This image was taken at a distance.
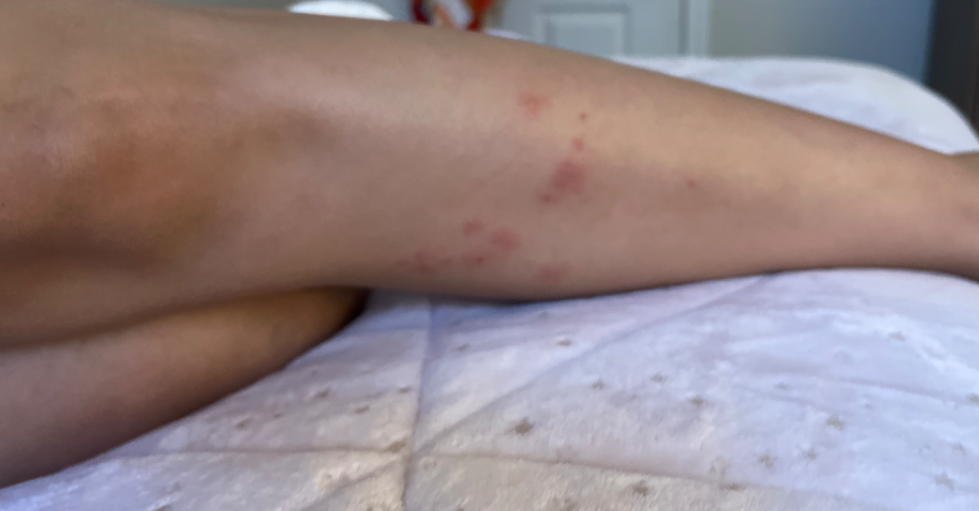| key | value |
|---|---|
| assessment | not assessable |